The subject is a male aged 60–69 · reported lesion symptoms include itching and burning · the patient described the issue as a rash · the photograph was taken at a distance · located on the front of the torso, back of the hand, back of the torso and arm · the contributor notes the lesion is raised or bumpy — 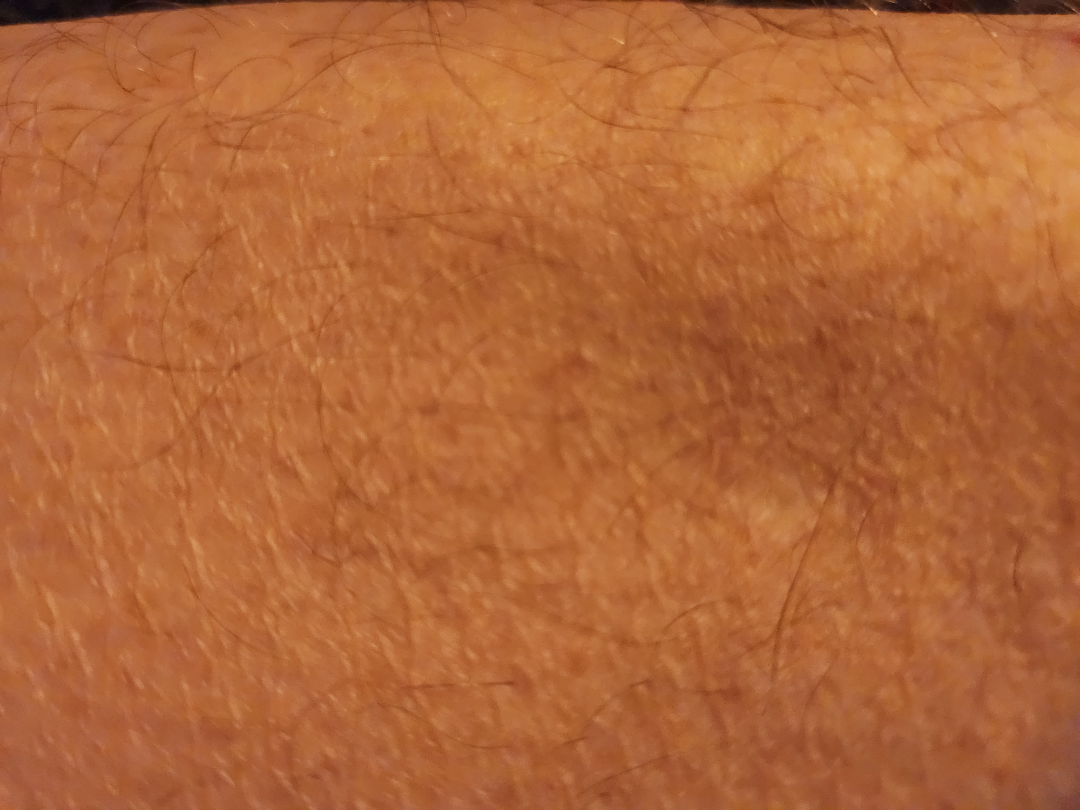Three dermatologists independently reviewed the case: the leading consideration is Dermatofibroma; an alternative is Insect Bite.